This image was taken at a distance: 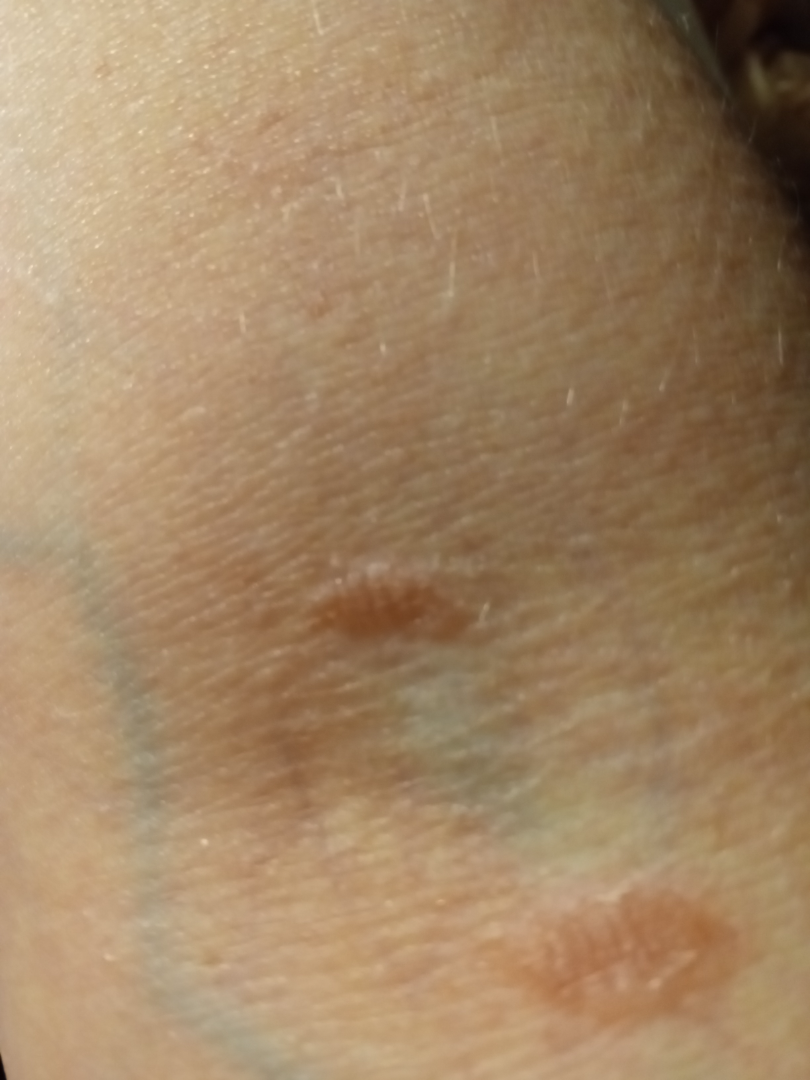No differential diagnosis could be assigned on photographic review.